A dermoscopy image of a single skin lesion: 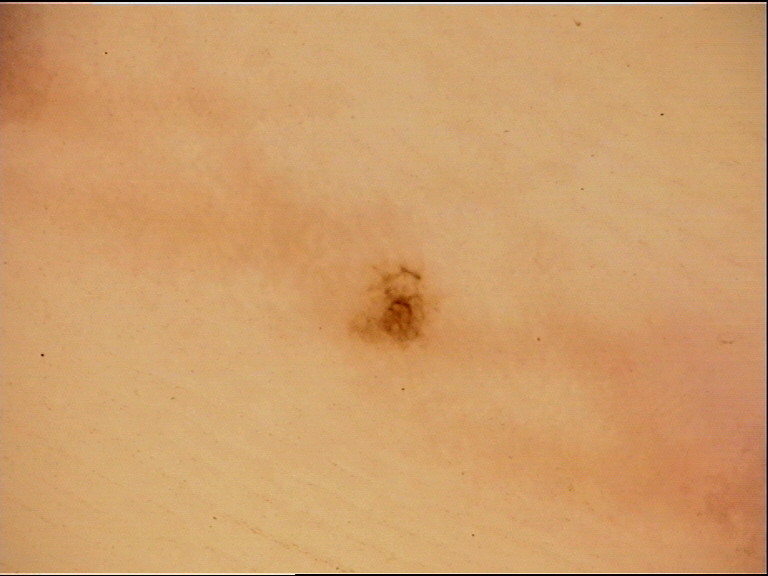Impression:
Diagnosed as an acral dysplastic junctional nevus.